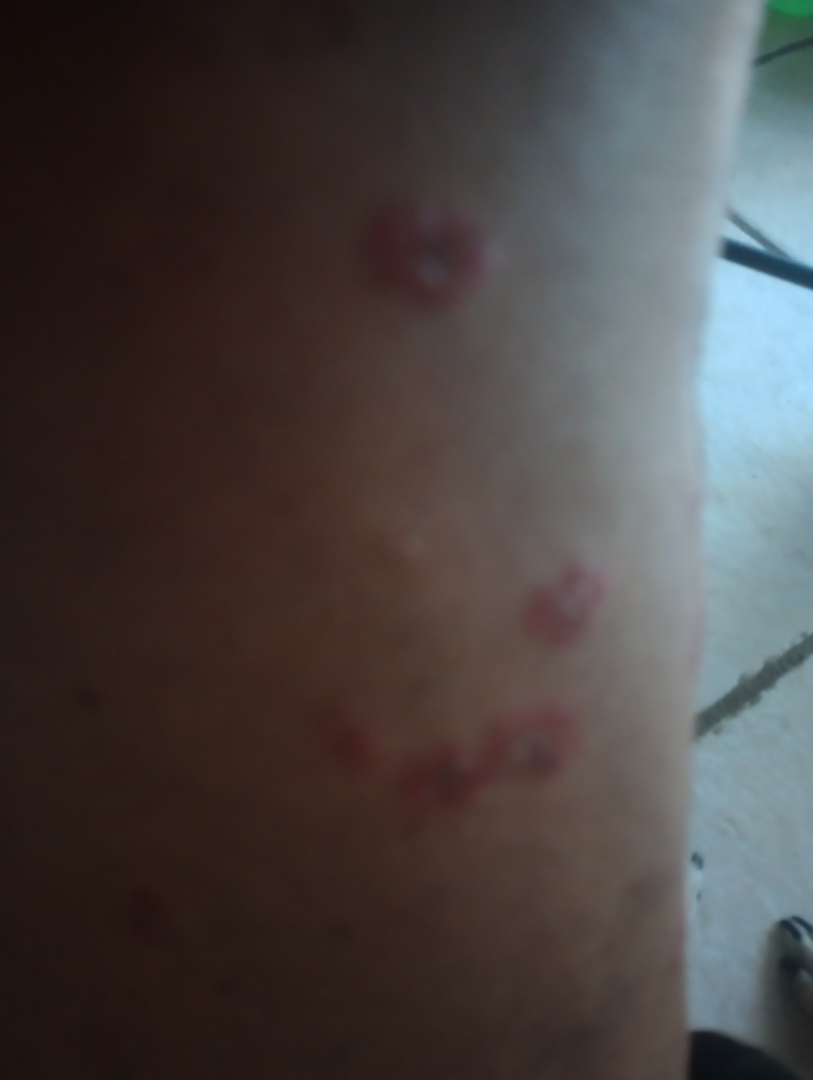<report>
<shot_type>close-up</shot_type>
<differential>
  <Pityriasis rosea>0.55</Pityriasis rosea>
  <Eczema>0.27</Eczema>
  <Erythema multiforme>0.18</Erythema multiforme>
</differential>
</report>